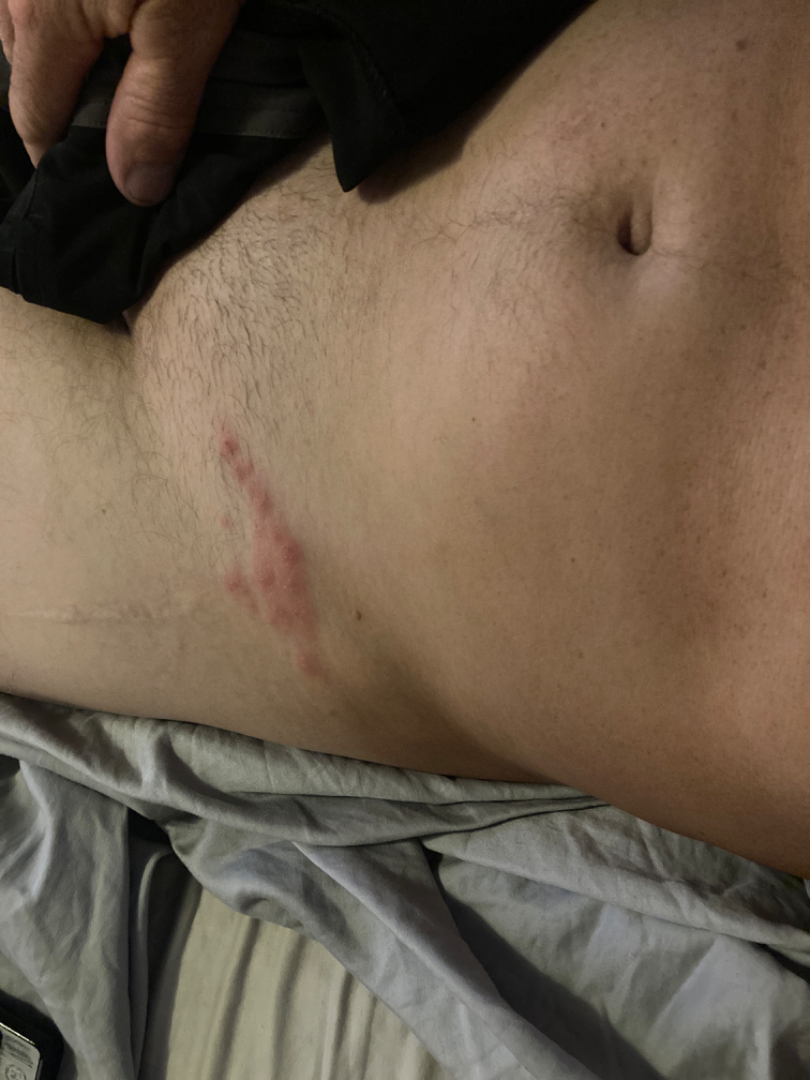History: The patient described the issue as a rash. The patient is 40–49, male. Fitzpatrick IV. This image was taken at a distance. Texture is reported as raised or bumpy and fluid-filled. The lesion is associated with bothersome appearance. The patient notes the condition has been present for about one day. Impression: The reviewer's impression was Herpes Zoster.